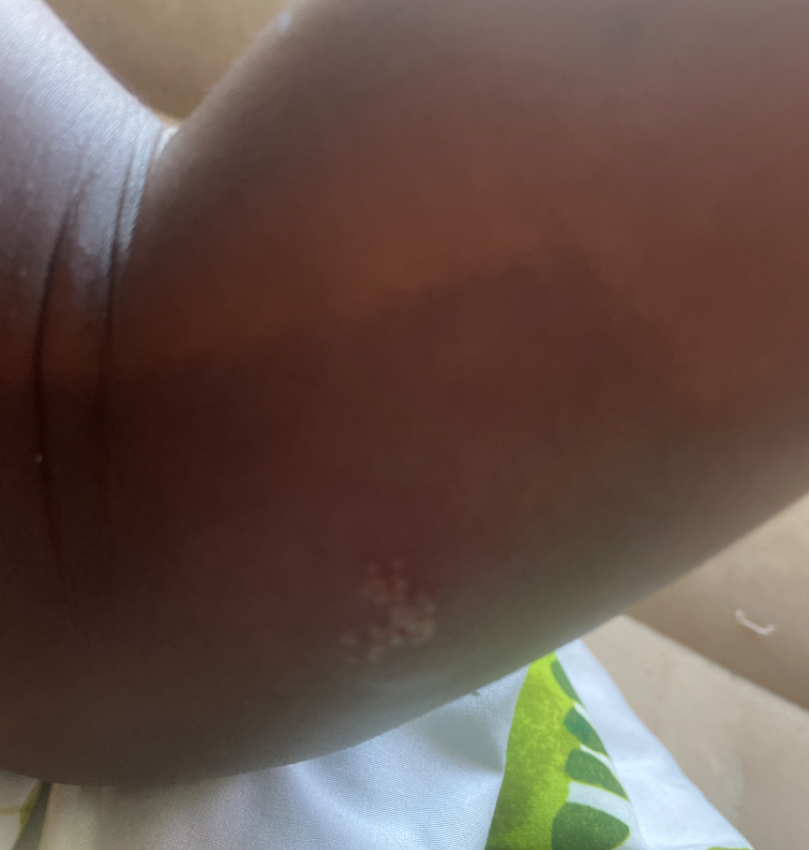Female patient, age 18–29. The arm is involved. The photo was captured at an angle. Consistent with Herpes Simplex.